A dermoscopic image of a skin lesion: 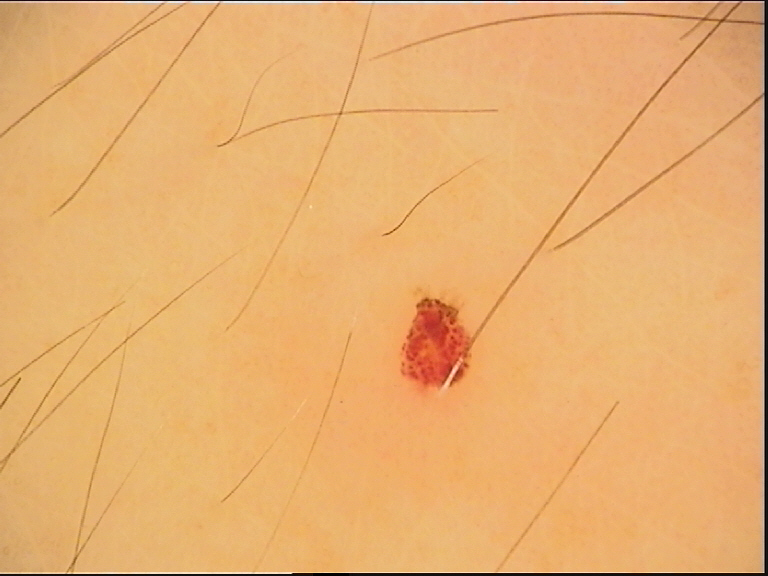Impression: The diagnostic label was a vascular lesion — a hemangioma.